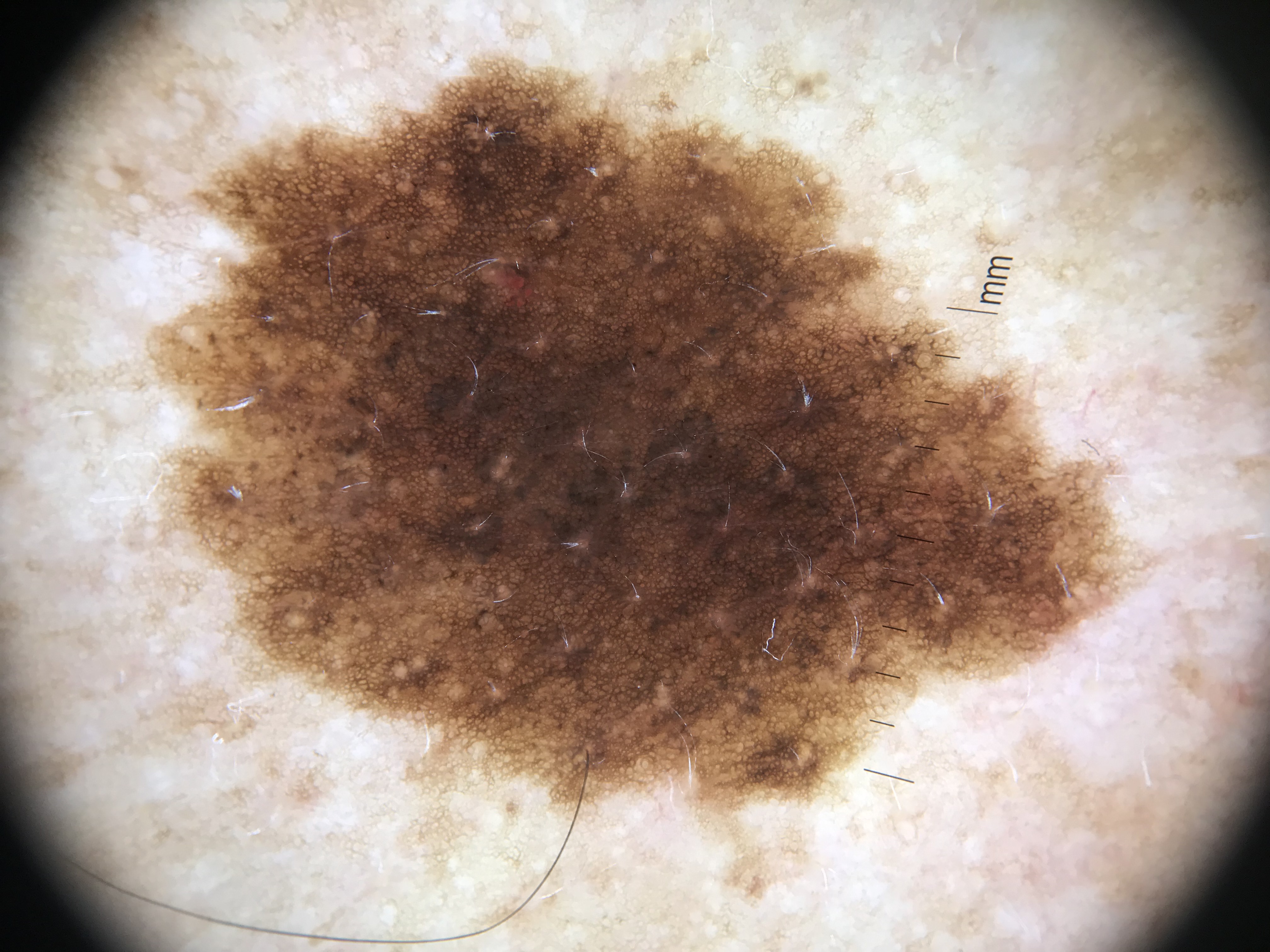Labeled as a dysplastic compound nevus.